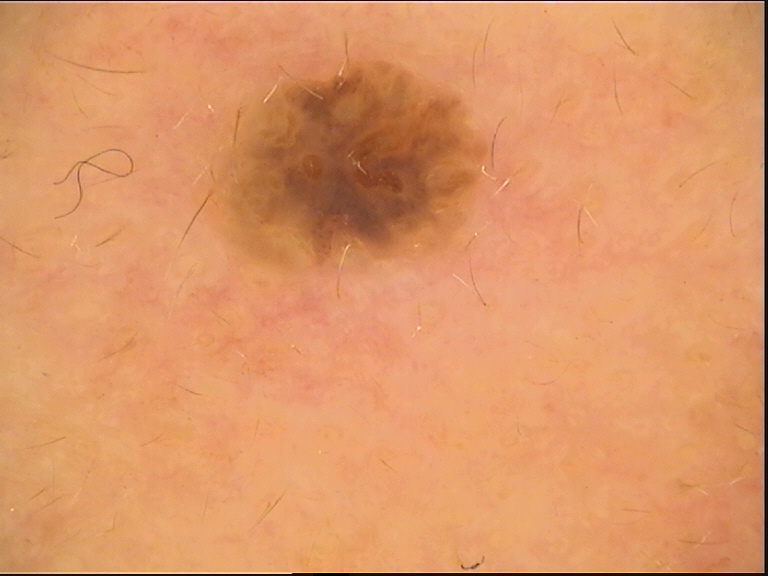{
  "diagnosis": {
    "name": "compound nevus",
    "code": "cb",
    "malignancy": "benign",
    "super_class": "melanocytic",
    "confirmation": "expert consensus"
  }
}